This image was taken at a distance; the front of the torso, head or neck, arm and back of the torso are involved:
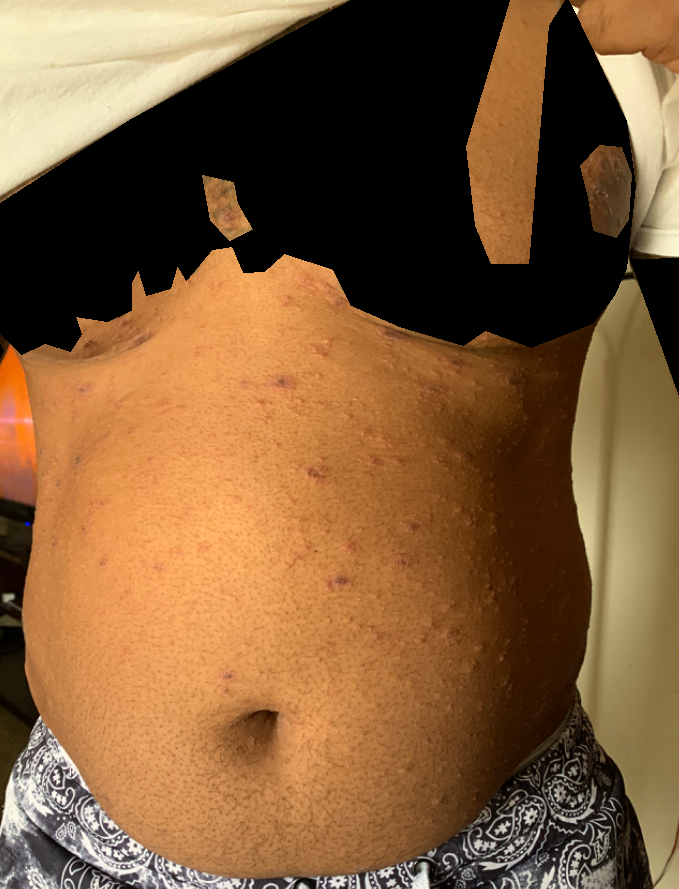The reviewing dermatologist's impression was: the leading consideration is Erythema multiforme; the differential also includes Pityriasis lichenoides; less likely is Drug Rash.